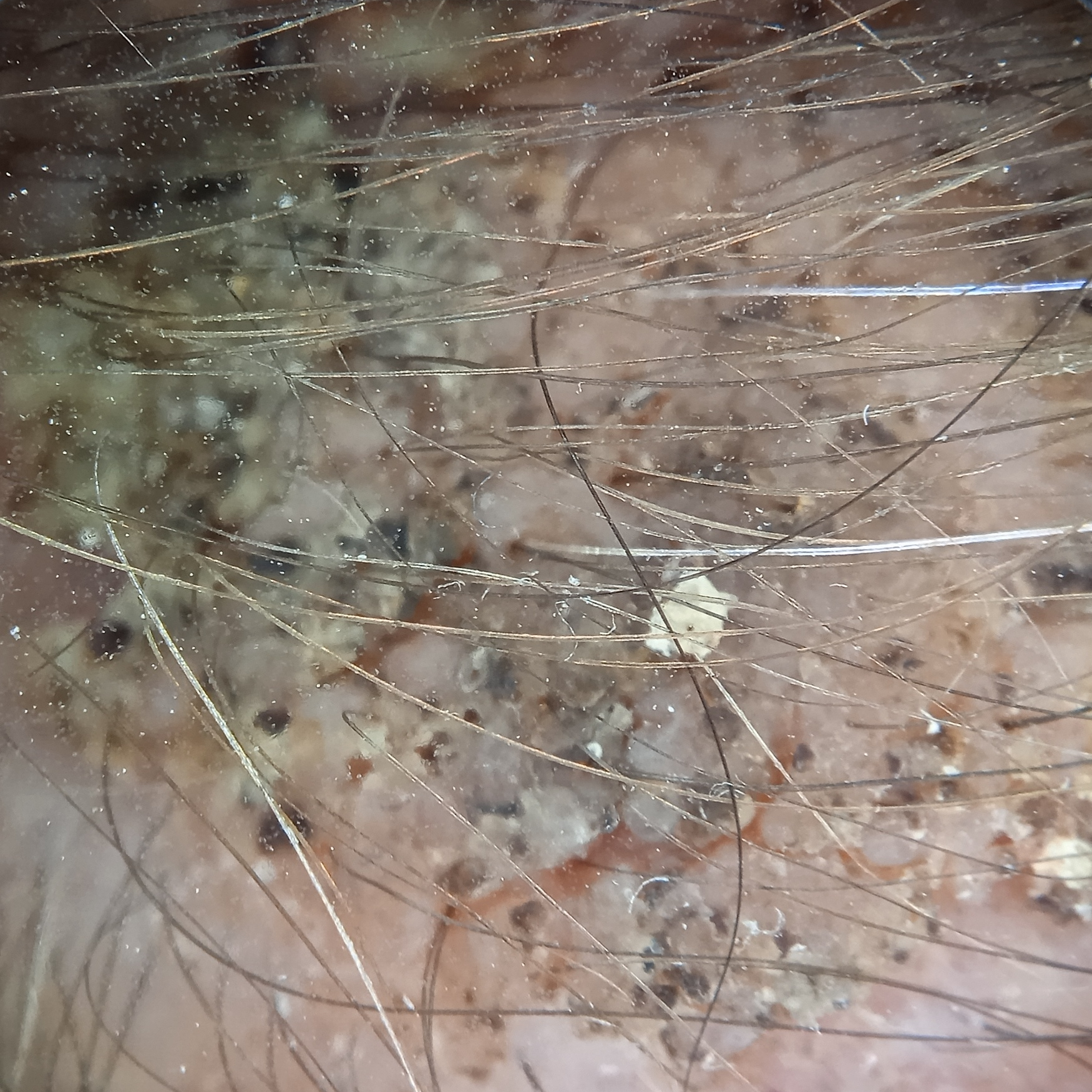Case summary: A skin lesion imaged with a dermatoscope. The patient says their skin tans without first burning. Acquired for a research image collection, with no referral diagnosis. The patient describes having a moderate number of moles. The lesion involves the head. The lesion measures approximately 19.2 mm. Conclusion: The consensus diagnosis for this lesion was a seborrheic keratosis.